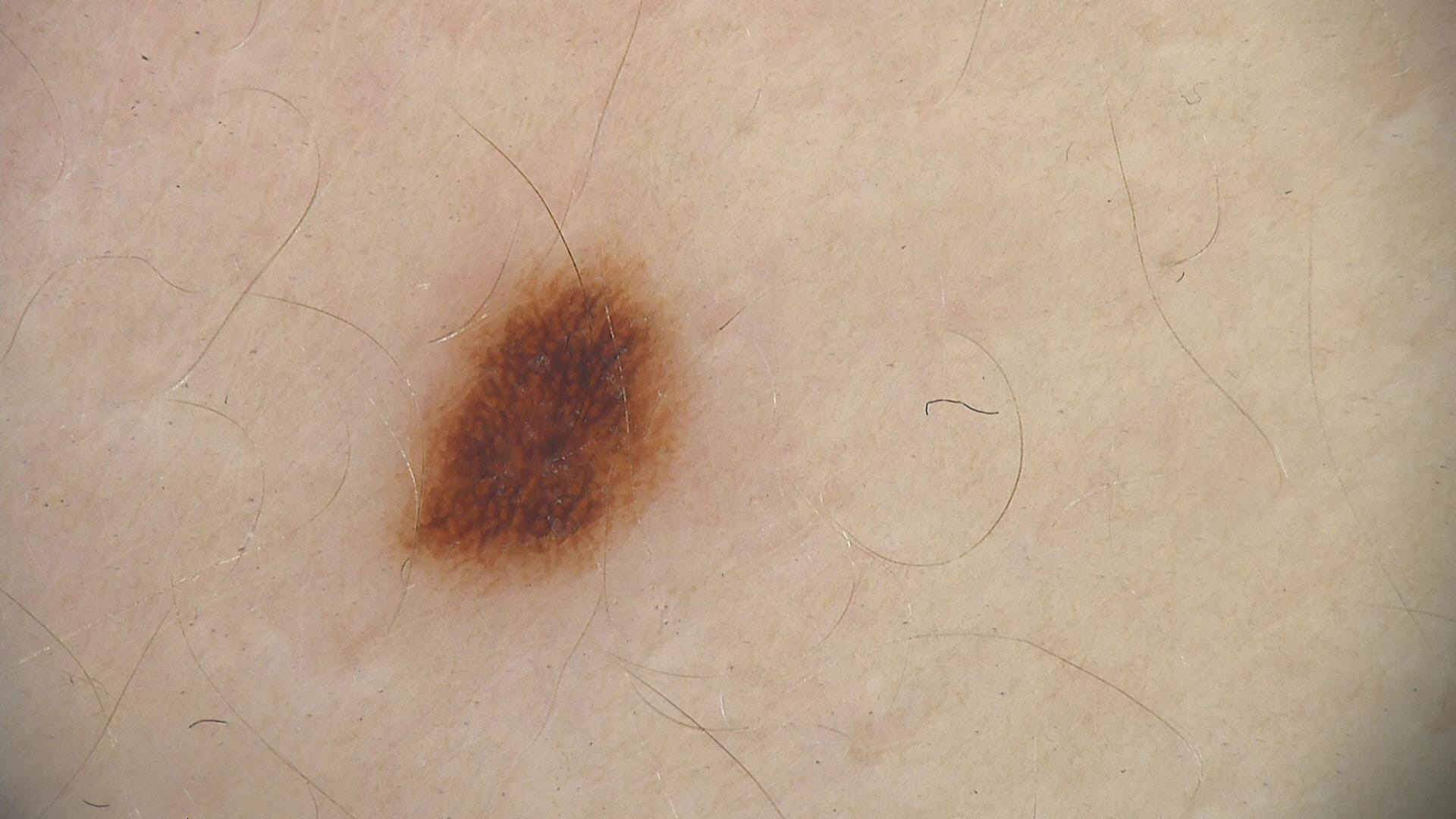modality: dermatoscopy | diagnostic label: dysplastic junctional nevus (expert consensus).